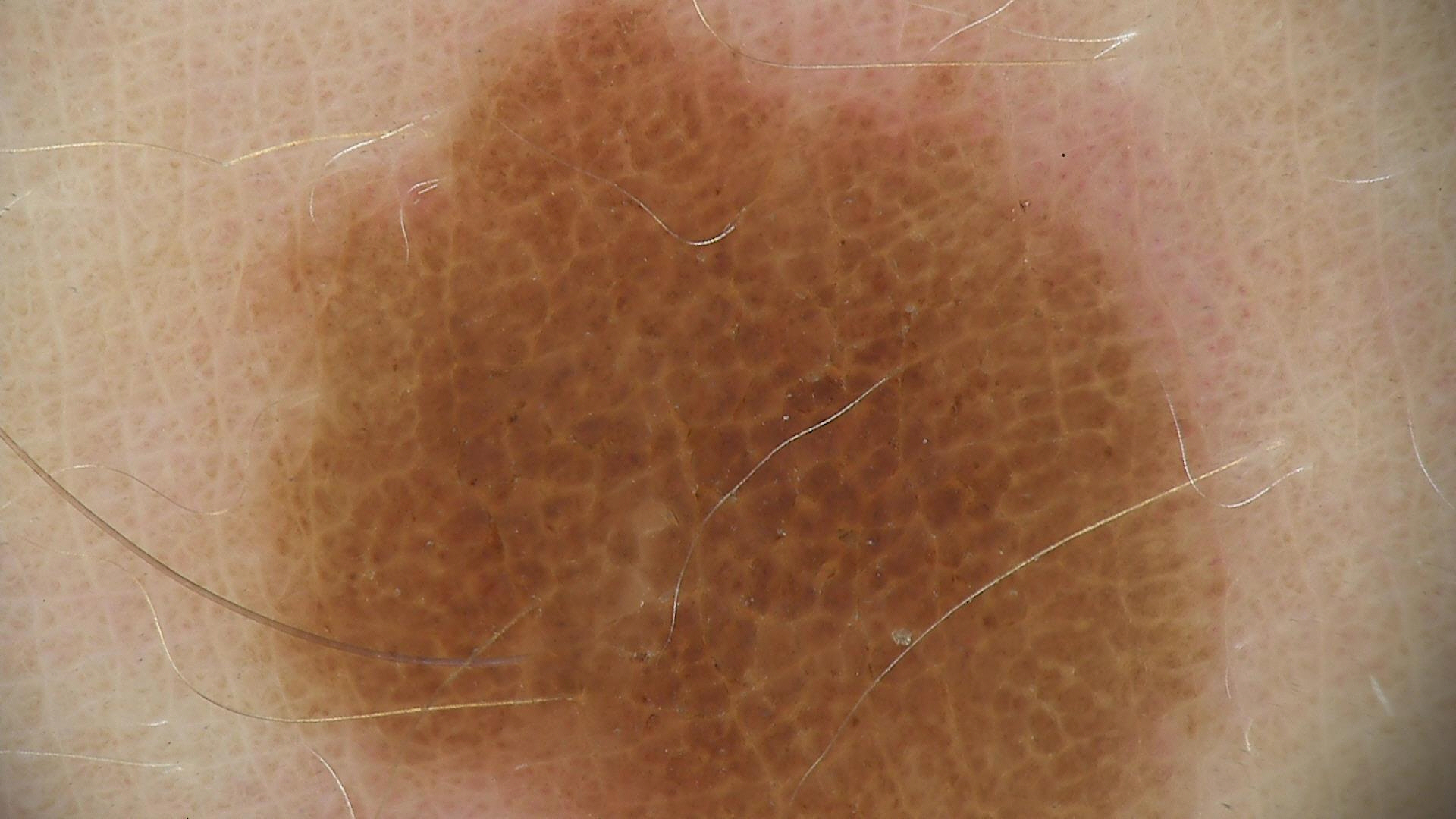imaging=dermoscopy
diagnosis=dysplastic compound nevus (expert consensus)